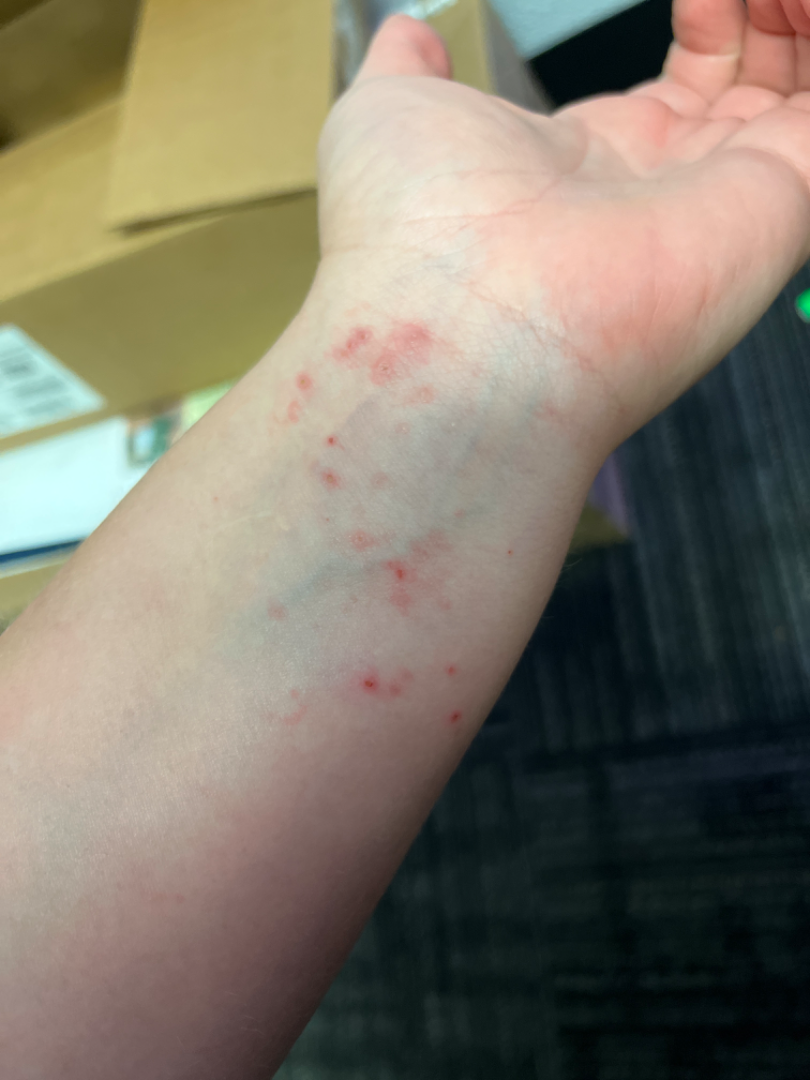dermatologist impression = Folliculitis, Allergic Contact Dermatitis and Irritant Contact Dermatitis were each considered, in no particular order.